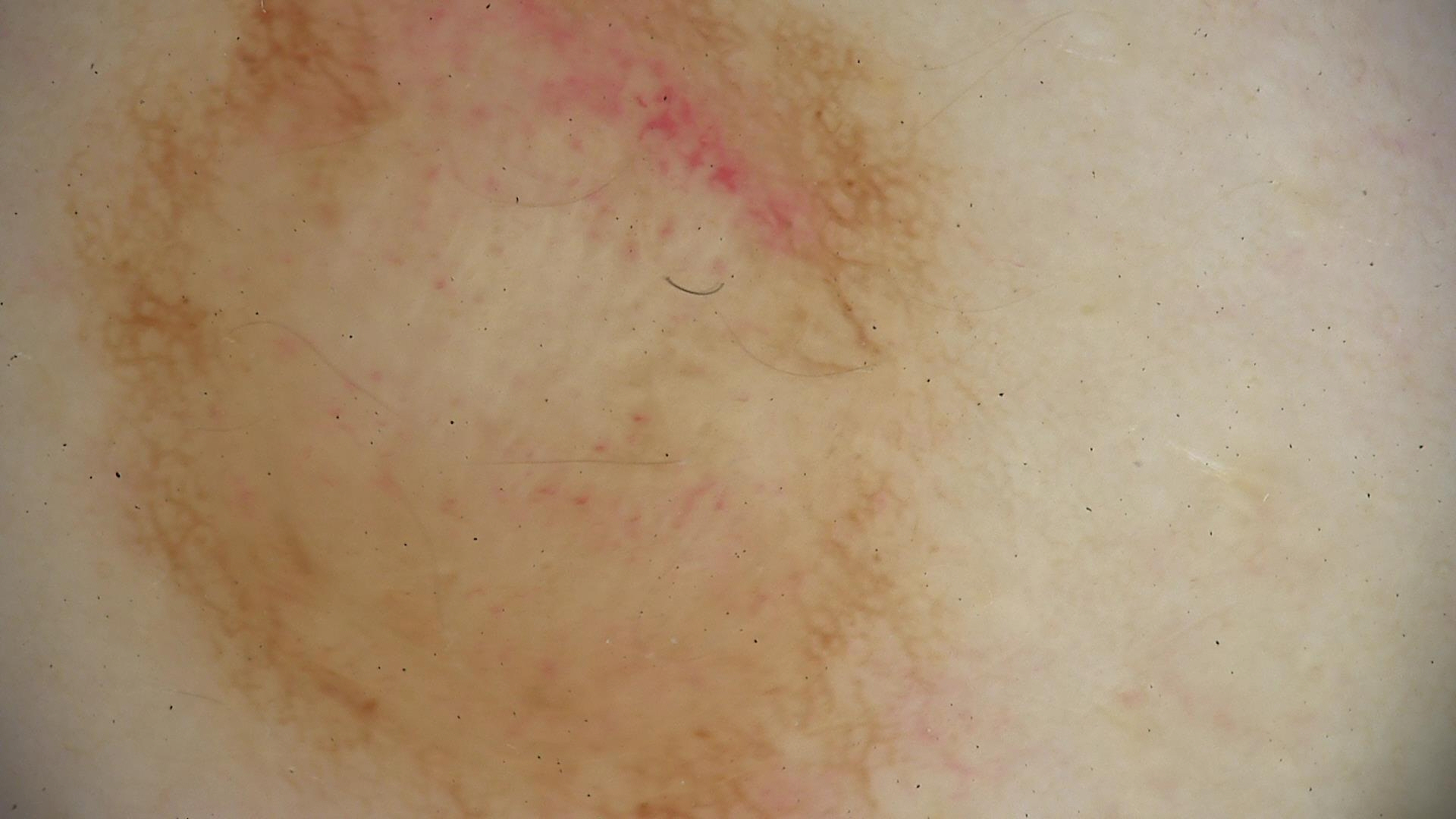Diagnosed as a dermal nevus.